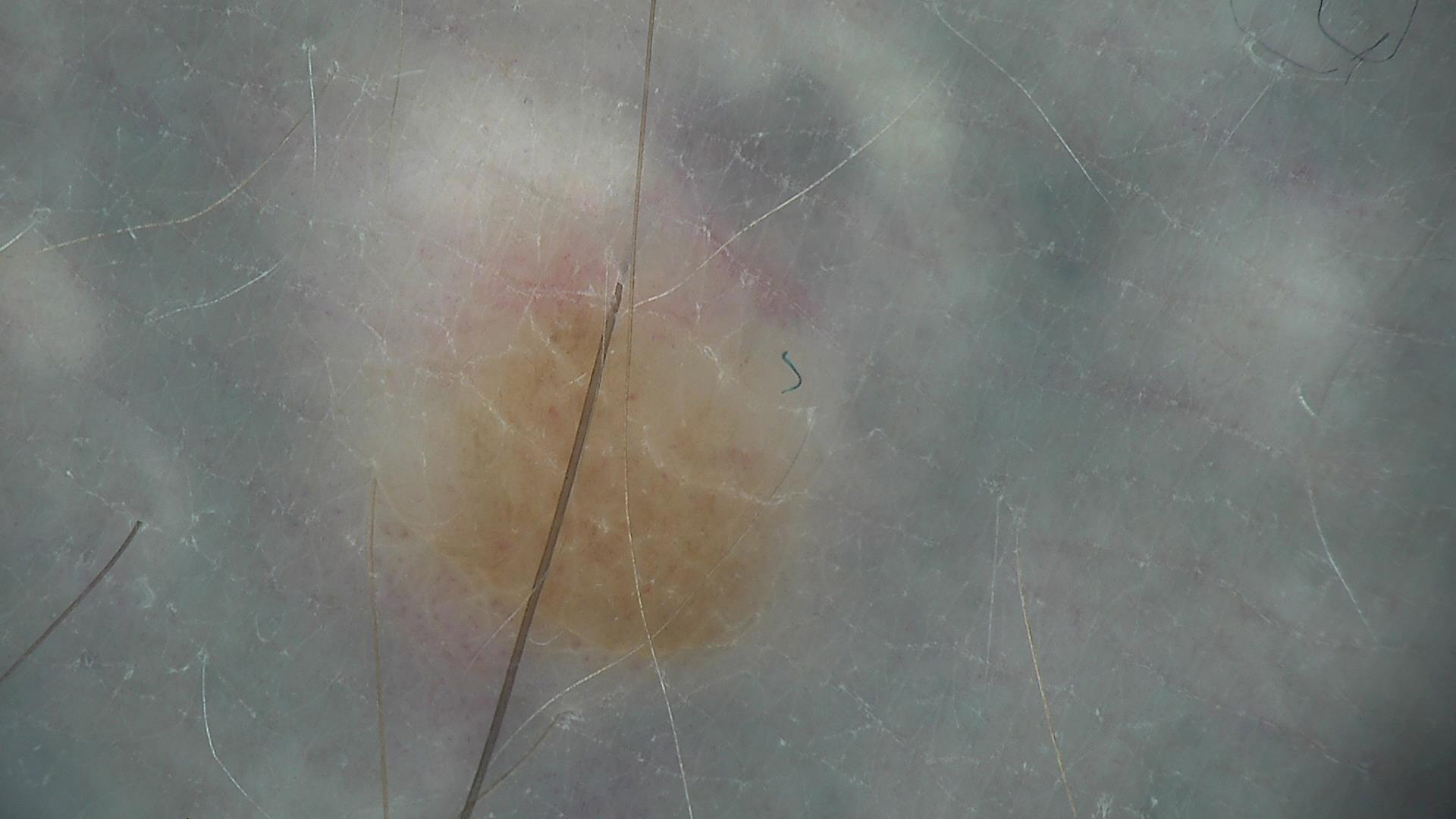Summary:
A skin lesion imaged with a dermatoscope.
Conclusion:
Diagnosed as a banal lesion — a dermal nevus.